The condition has been present for less than one week, the lesion is associated with itching, the leg is involved, no associated systemic symptoms reported, texture is reported as raised or bumpy, the contributor is a female aged 70–79, this image was taken at an angle: 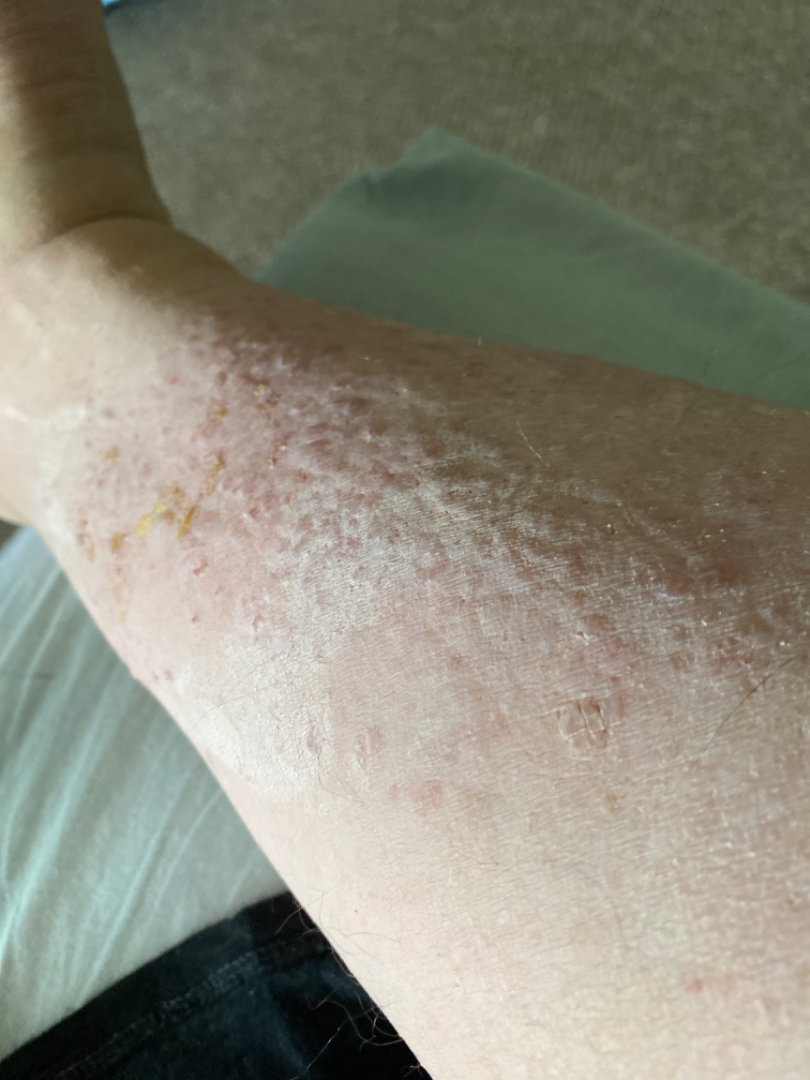impression = three dermatologists independently reviewed the case: the leading consideration is Stasis Dermatitis; also consider Pretibial myxedema; lower on the differential is Amyloidosis of skin.